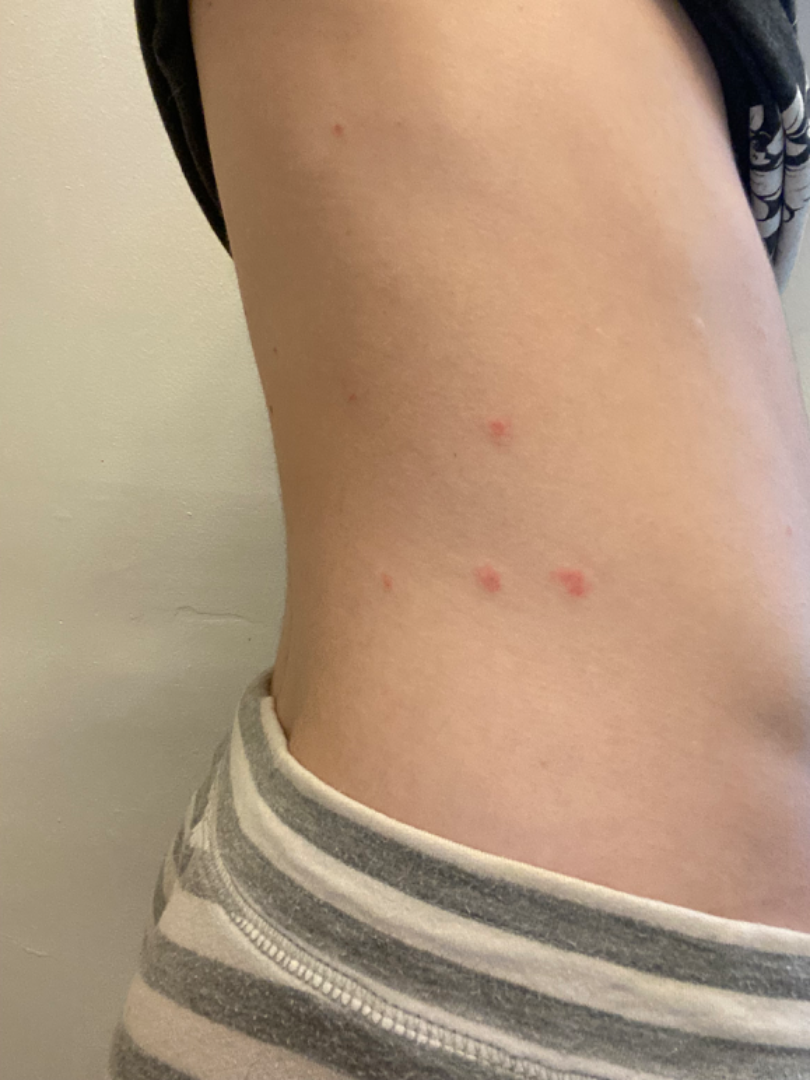{"assessment": "indeterminate from the photograph"}